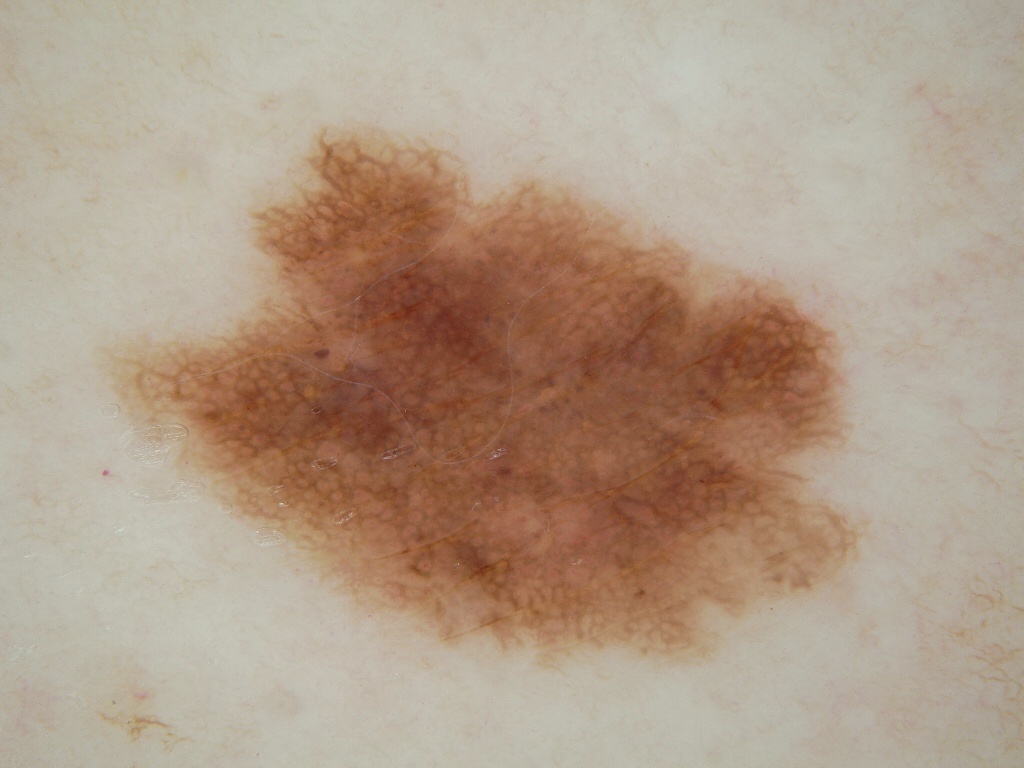A dermoscopic close-up of a skin lesion. A female subject, aged approximately 70. A prominent lesion filling much of the field. Dermoscopically, the lesion shows pigment network and globules; no milia-like cysts, negative network, or streaks. With coordinates (x1, y1, x2, y2), lesion location: <bbox>104, 124, 900, 669</bbox>. Expert review diagnosed this as a melanocytic nevus.